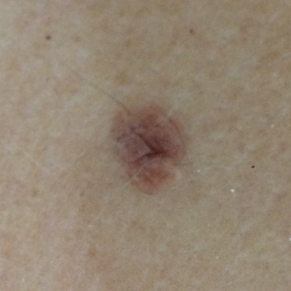patient = in their 50s | modality = smartphone clinical photo | anatomic site = the back | reported symptoms = bleeding, elevation, growth | impression = nevus (clinical consensus).